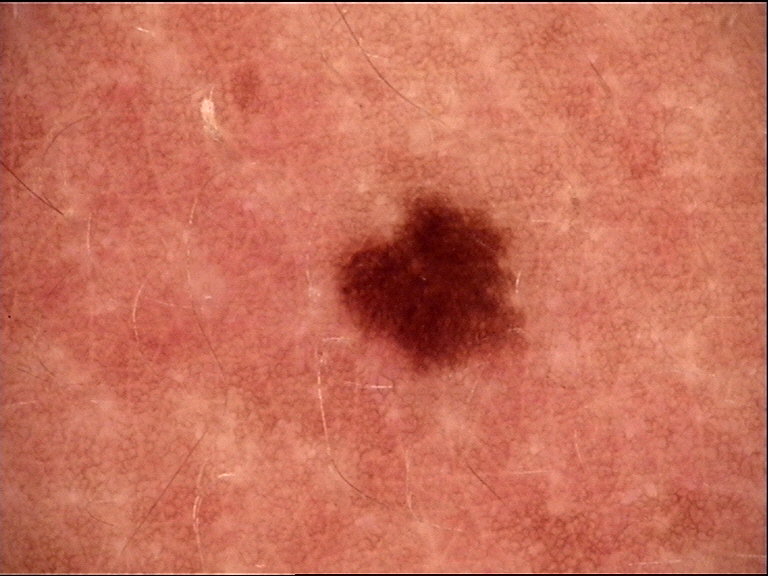A dermoscopic image of a skin lesion.
The diagnosis was a benign lesion — a dysplastic junctional nevus.